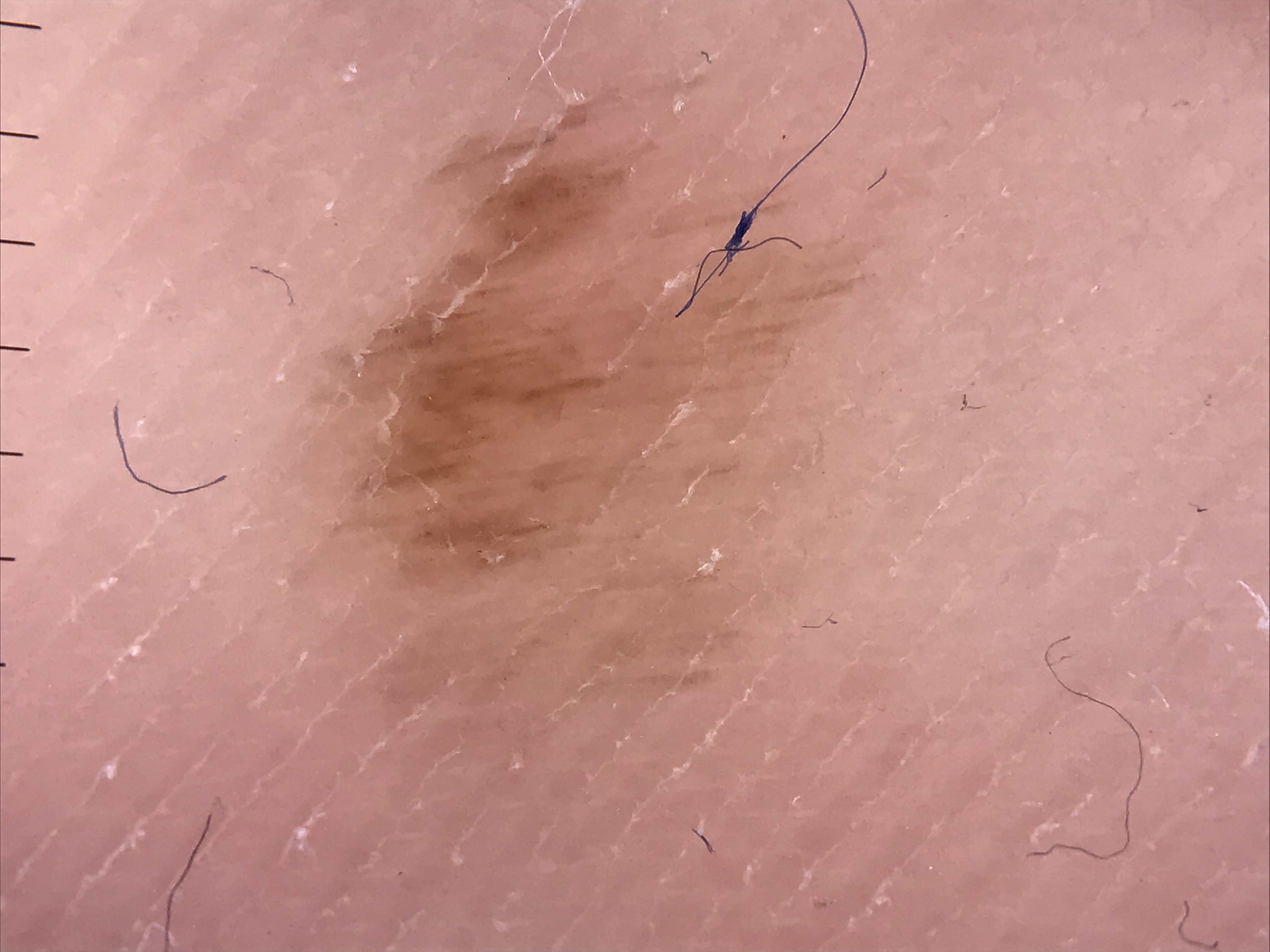Findings:
• label · acral junctional nevus (expert consensus)